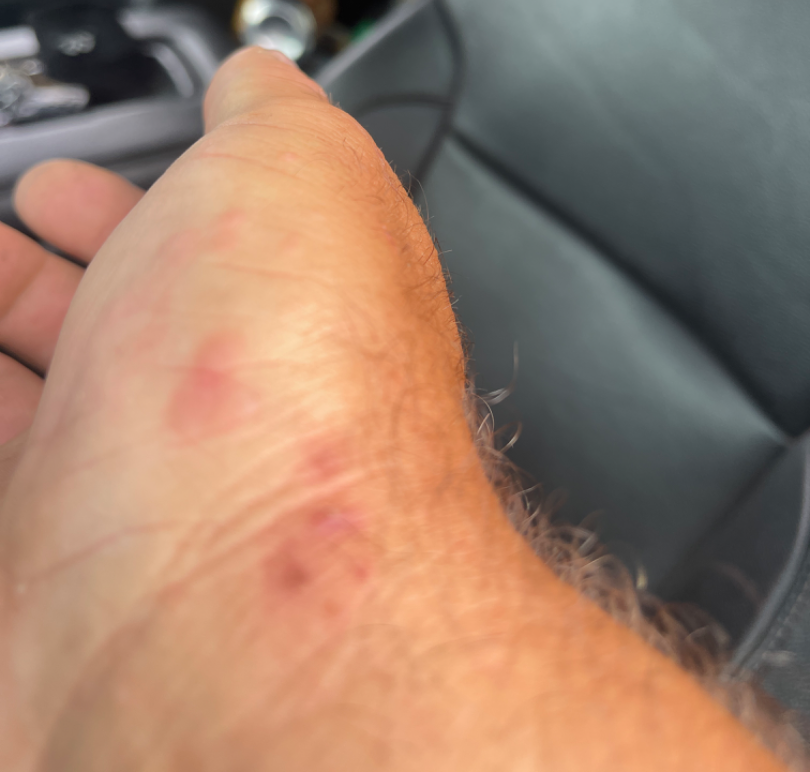Assessment: On remote dermatologist review: most consistent with Eczema; also consider Scabies; also on the differential is Allergic Contact Dermatitis.